A dermoscopic image of a skin lesion: 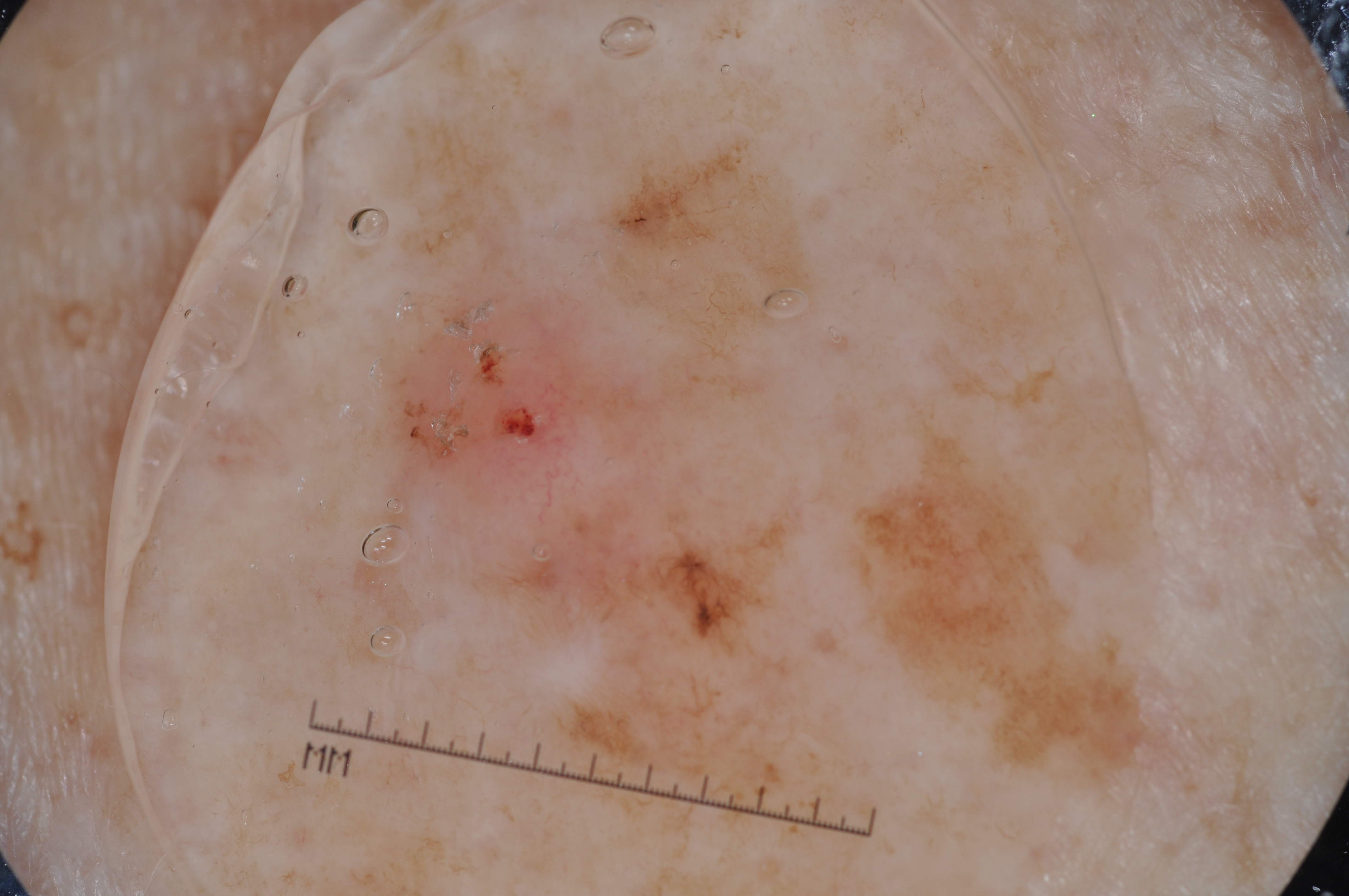As (left, top, right, bottom), the lesion spans 323 228 921 877. Dermoscopically, the lesion shows pigment network; no milia-like cysts, streaks, or negative network. The biopsy diagnosis was a melanoma, a malignant skin lesion.